Dermoscopy of a skin lesion:
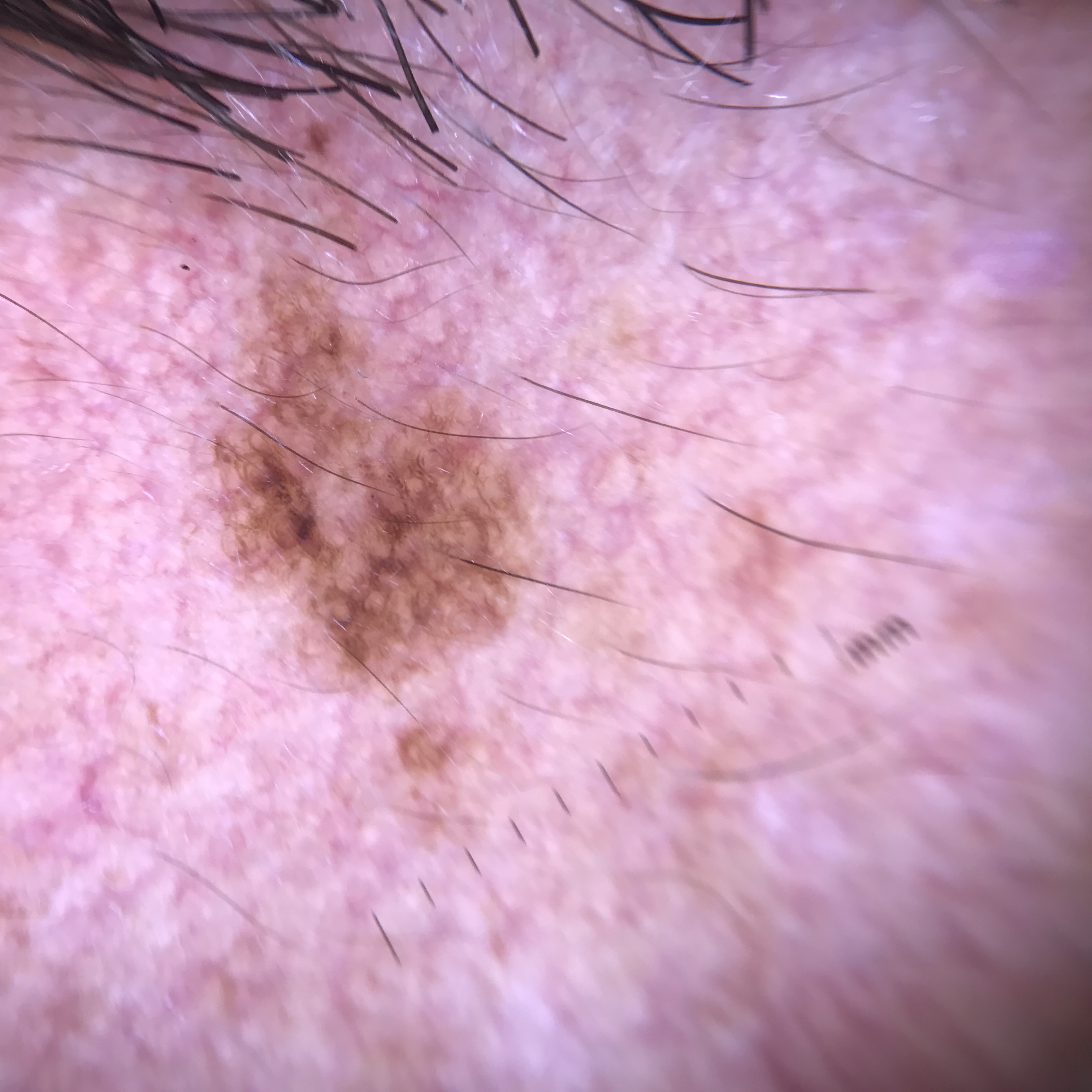Q: What is the diagnosis?
A: solar lentigo (expert consensus)